Female contributor, age 18–29; no relevant systemic symptoms; the contributor notes the lesion is rough or flaky and raised or bumpy; the palm is involved; the photo was captured at an angle; the condition has been present for less than one week; the lesion is associated with burning, itching and pain:
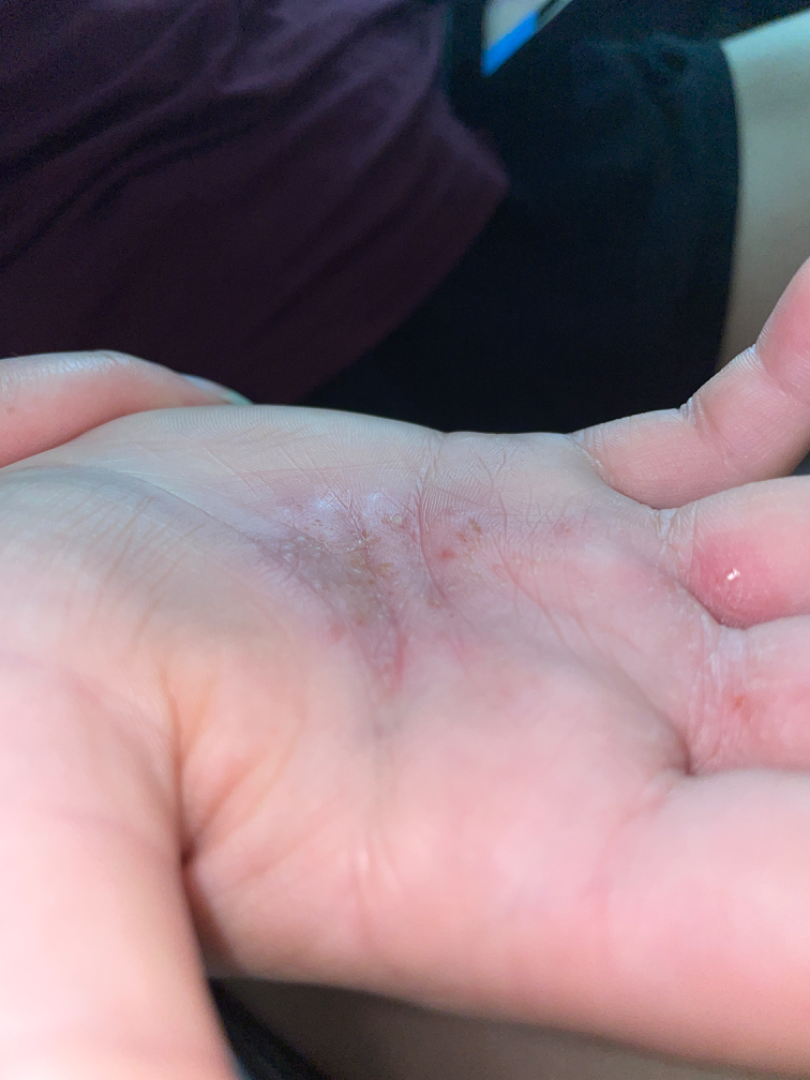Review:
On independent review by the dermatologists: the primary impression is Eczema; an alternative is Psoriasis; a remote consideration is Allergic Contact Dermatitis; less probable is Tinea.